A male patient 83 years old · the patient says their skin reddens with sun exposure · a macroscopic clinical photograph of a skin lesion · acquired for a research image collection, with no referral diagnosis · by self-report, no immunosuppression:
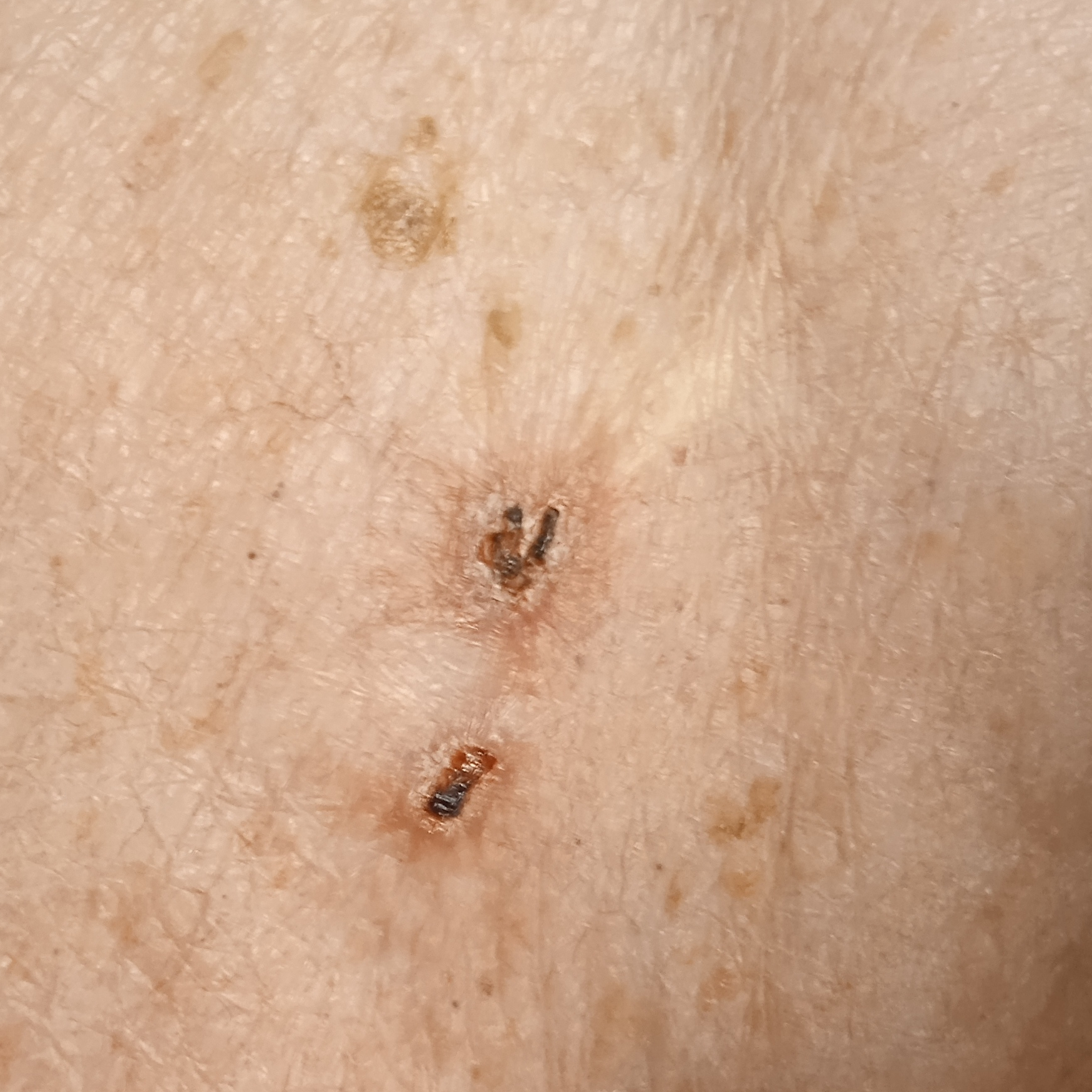lesion_location: the back
lesion_size:
  diameter_mm: 9.5
diagnosis:
  name: basal cell carcinoma
  malignancy: malignant